A dermoscopic photograph of a skin lesion:
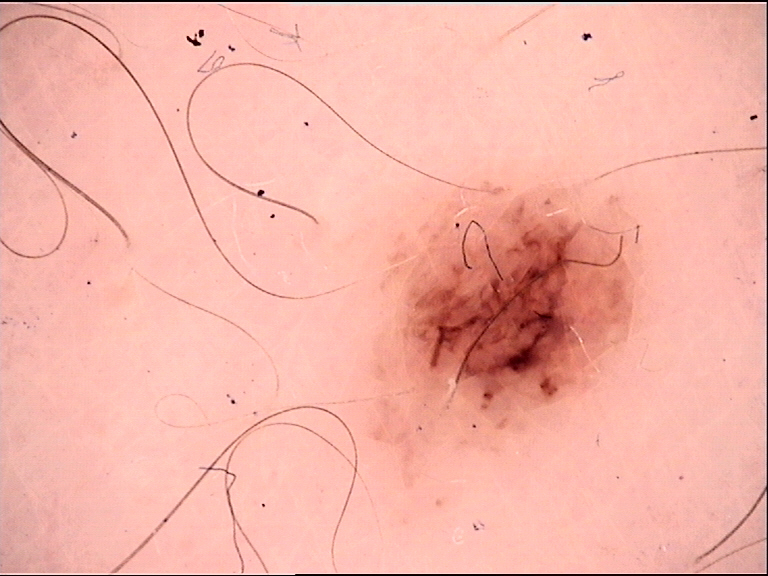Impression: Classified as a dysplastic compound nevus.